This image was taken at an angle — 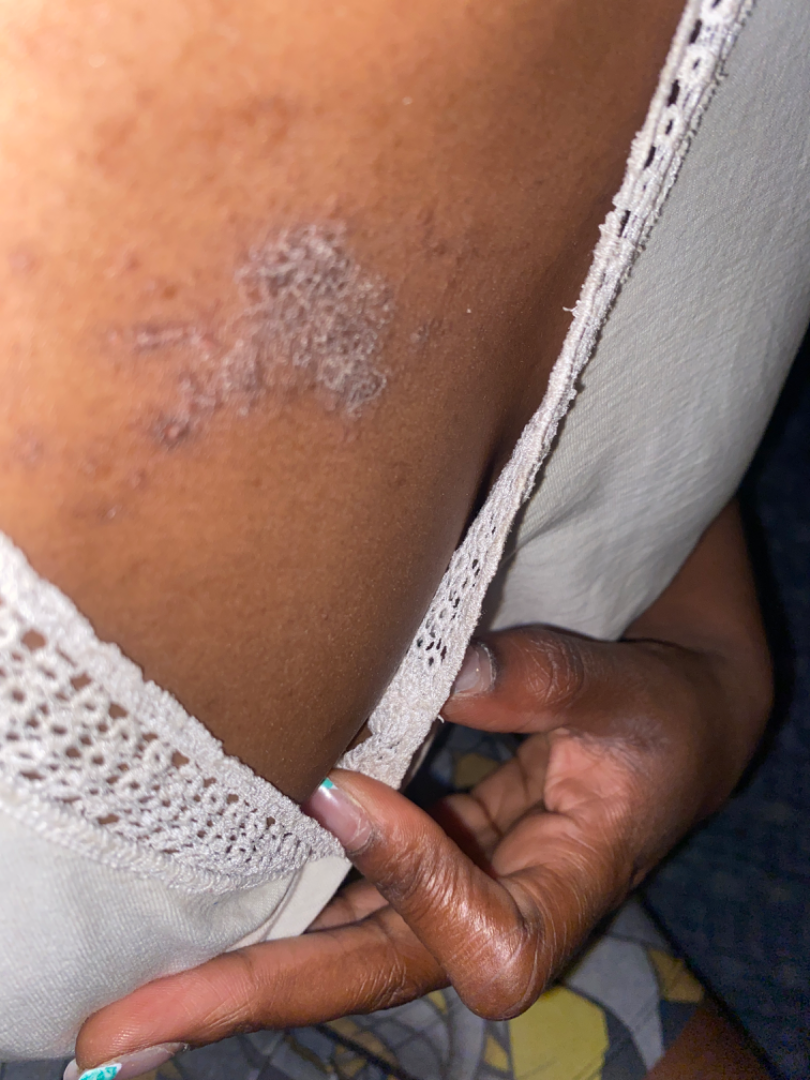| feature | finding |
|---|---|
| dermatologist impression | the differential includes Lichen planus/lichenoid eruption and Chronic dermatitis, NOS, with no clear leading consideration |